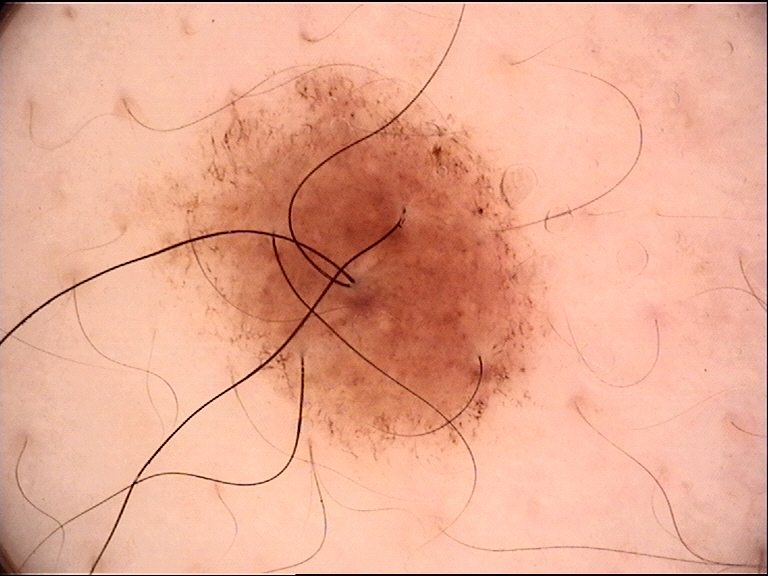A dermoscopic photograph of a skin lesion.
Labeled as a benign lesion — a dysplastic compound nevus.